The photograph is a close-up of the affected area:
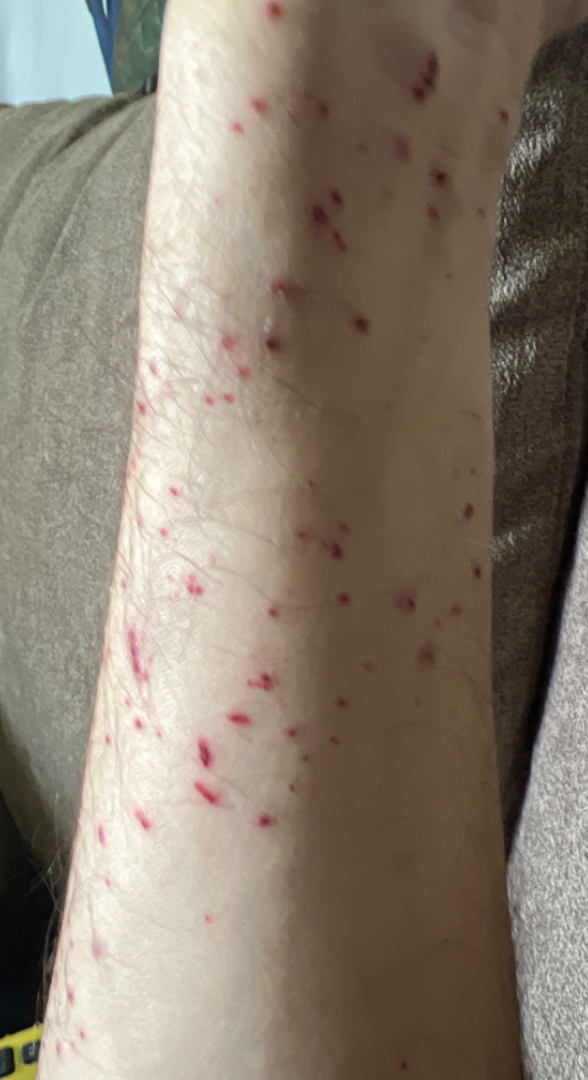The skin findings could not be characterized from the image.